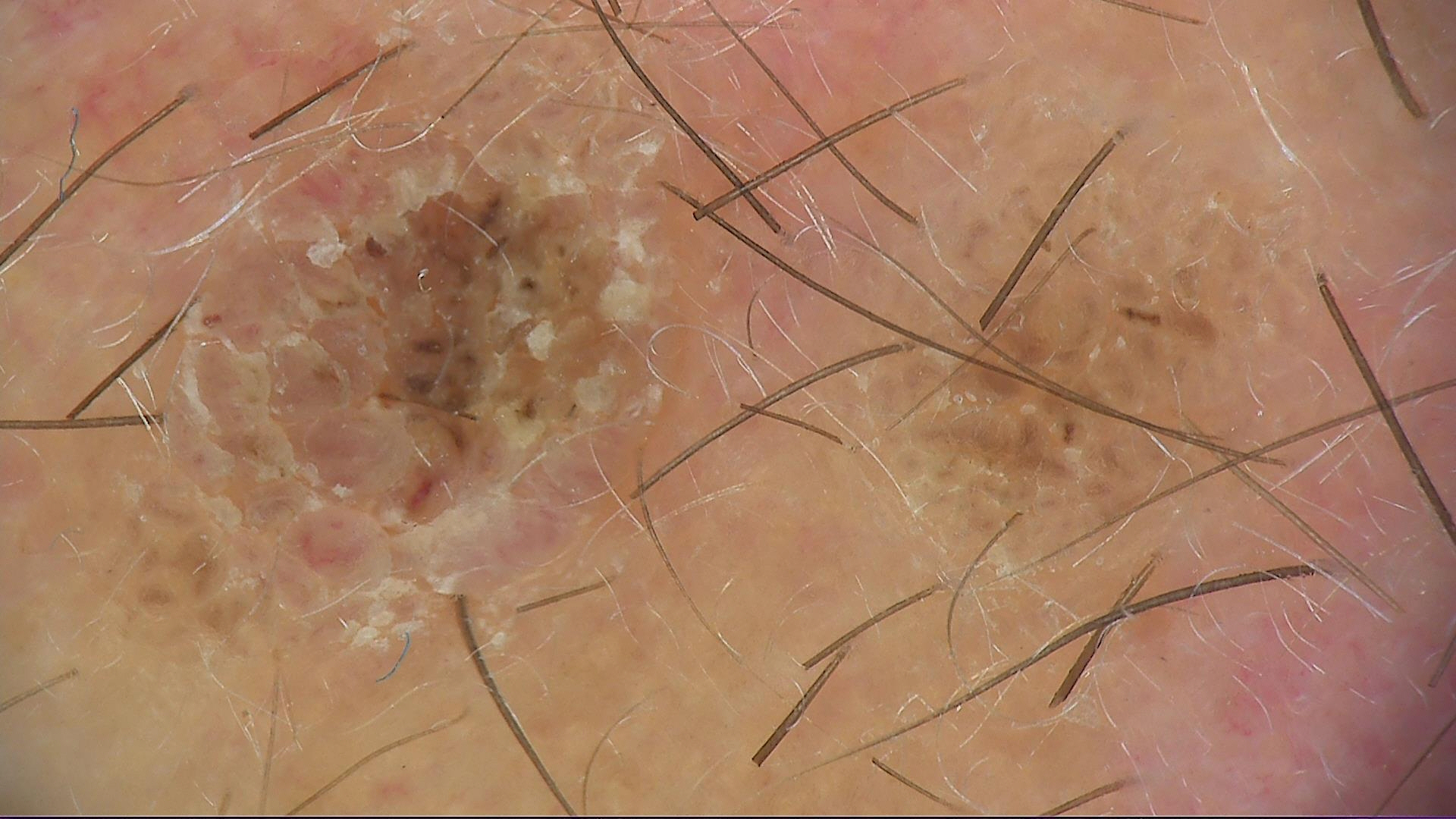Classified as a seborrheic keratosis.